The condition has been present for one to four weeks. The lesion is described as raised or bumpy. Skin tone: Fitzpatrick phototype V; lay reviewers estimated Monk skin tone scale 5 (US pool) or 4 (India pool). The contributor is 18–29, female. This is a close-up image. No constitutional symptoms were reported:
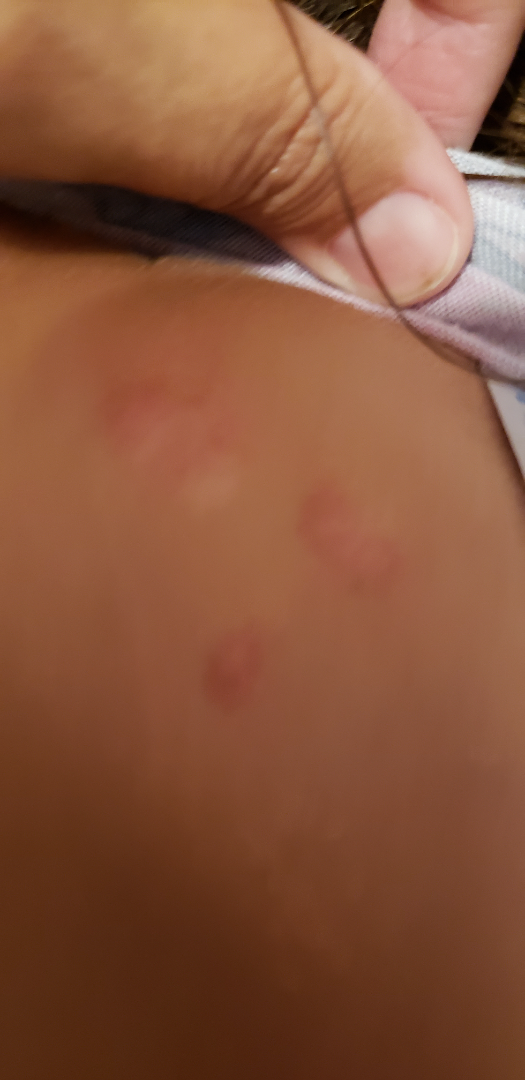{"assessment": "could not be assessed"}